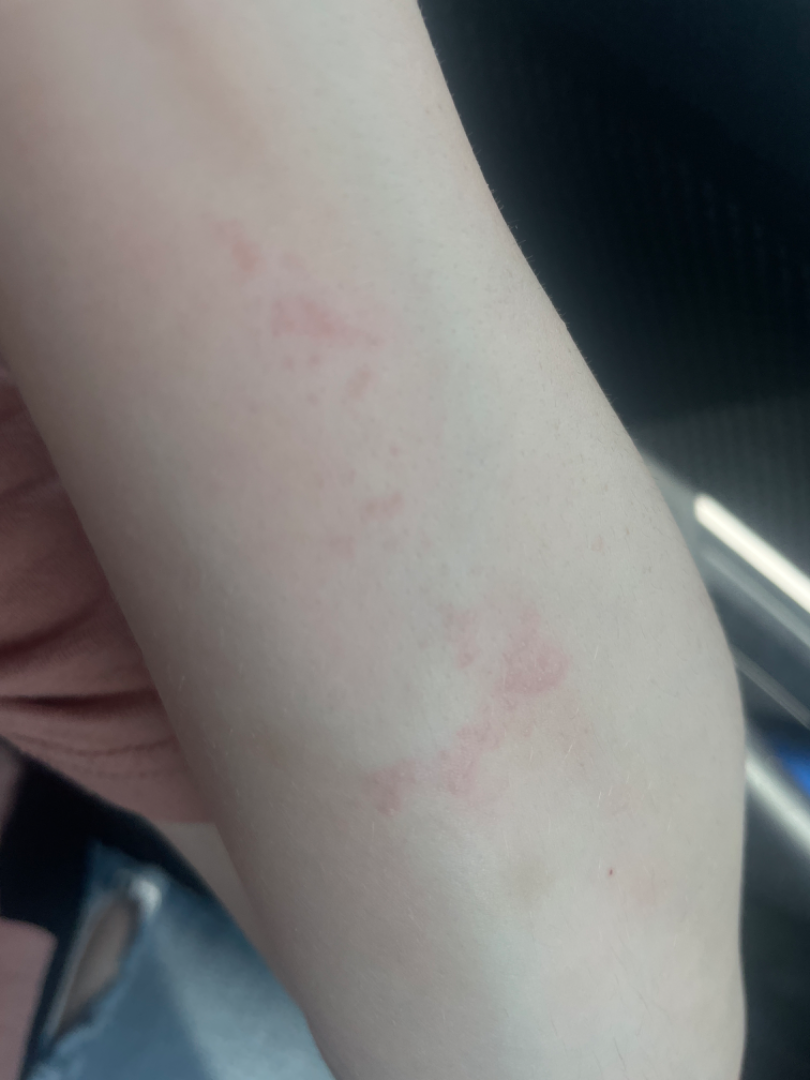Review: The case was difficult to assess from the available photograph. Patient information: Texture is reported as raised or bumpy. This is a close-up image. Reported duration is about one day. The affected area is the arm.